A dermoscopy image of a single skin lesion: 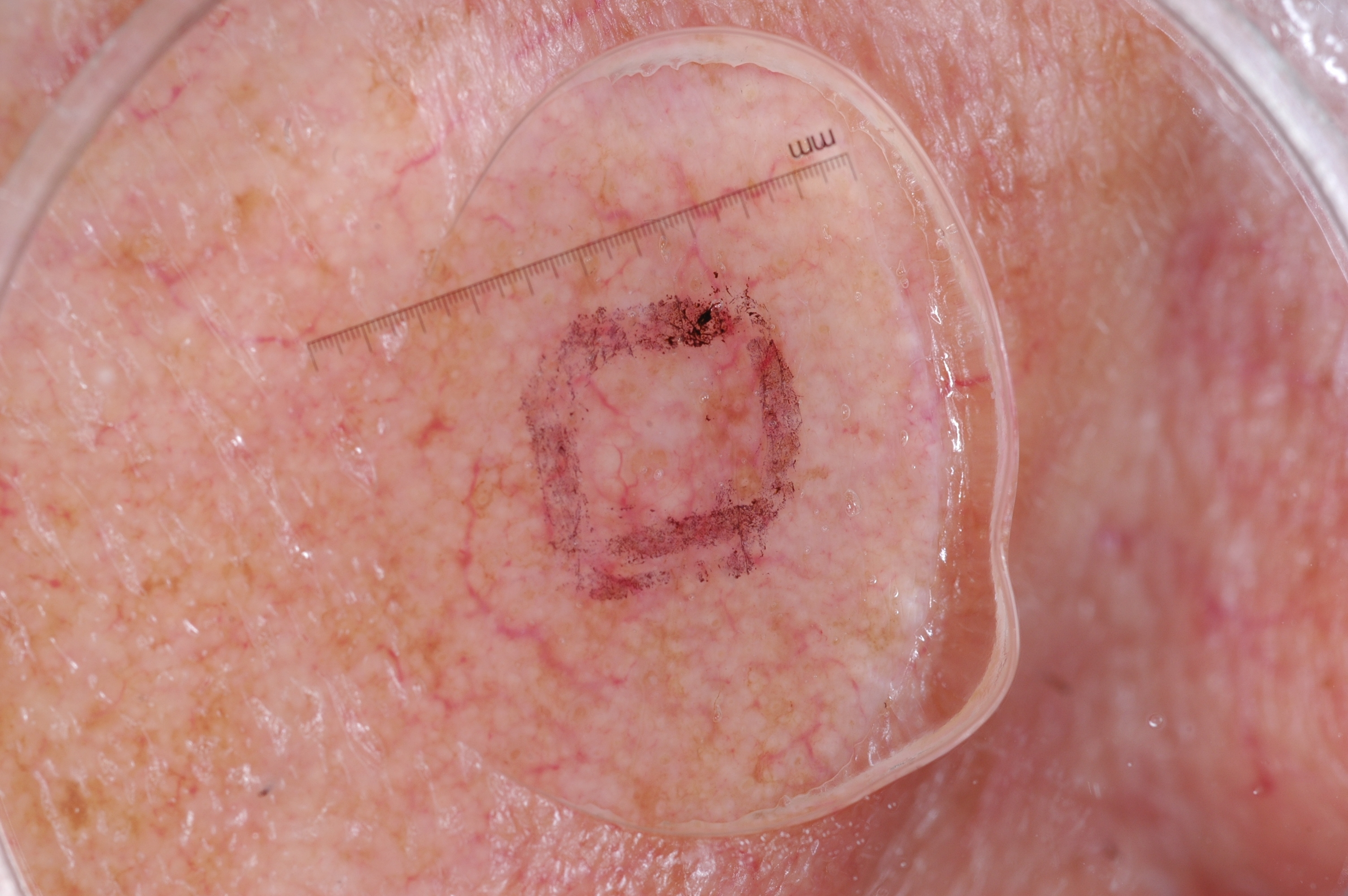absent dermoscopic findings: pigment network, streaks, milia-like cysts, and negative network
lesion location: 581, 353, 741, 523
diagnosis: a seborrheic keratosis, a benign skin lesion